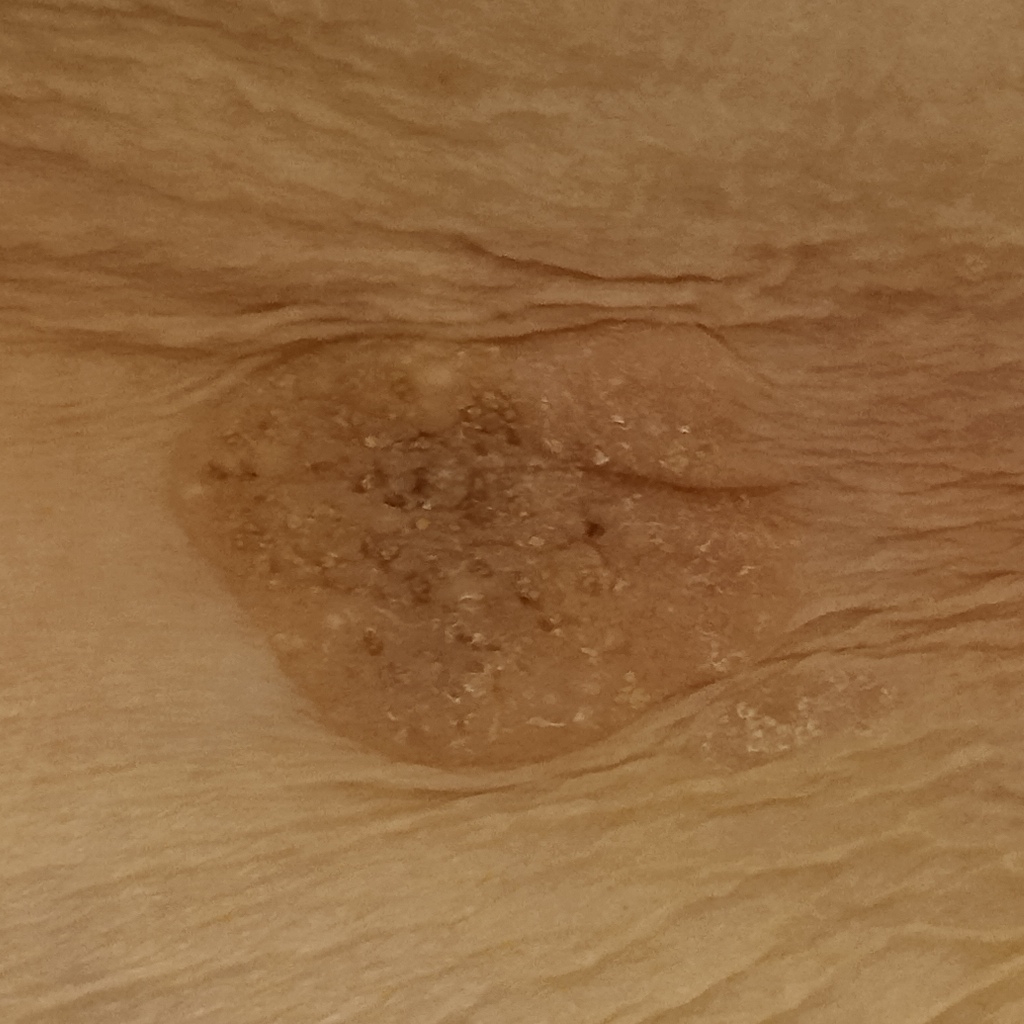| field | value |
|---|---|
| imaging | clinical photo |
| referral context | research study (no referral diagnosis) |
| relevant history | no immunosuppression, no sunbed use |
| subject | female, 81 years old |
| sun reaction | skin reddens painfully with sun exposure |
| nevus count | a moderate number of melanocytic nevi |
| body site | the torso |
| size | 31 mm |
| diagnostic label | seborrheic keratosis (dermatologist consensus) |